The photograph was taken at an angle: 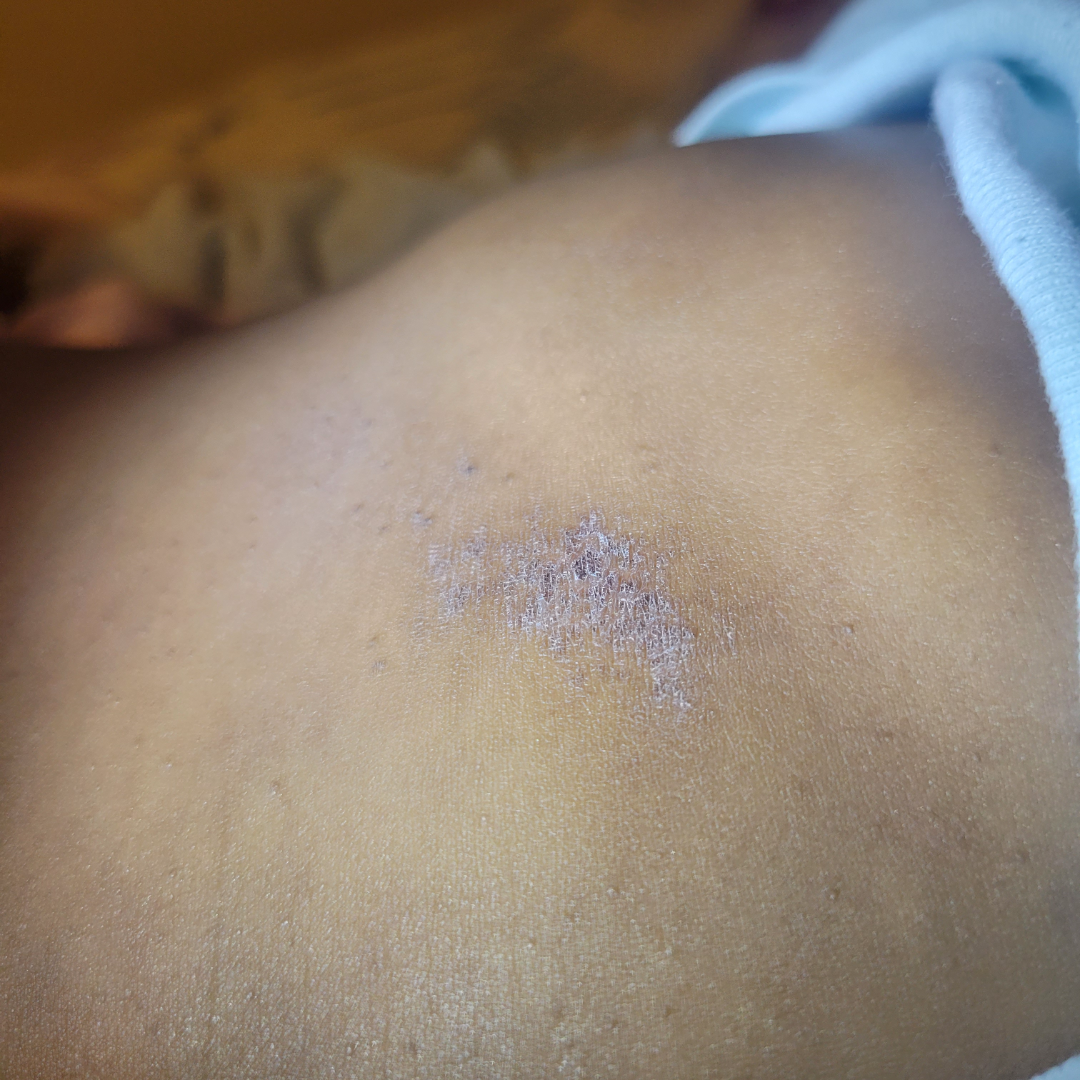Notes:
– differential diagnosis · most consistent with Chronic dermatitis, NOS